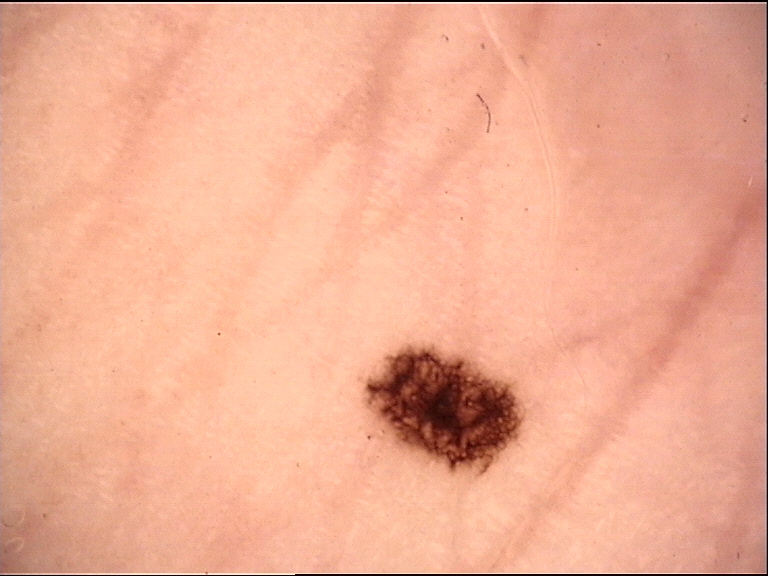A dermoscopy image of a single skin lesion. Labeled as an acral dysplastic junctional nevus.